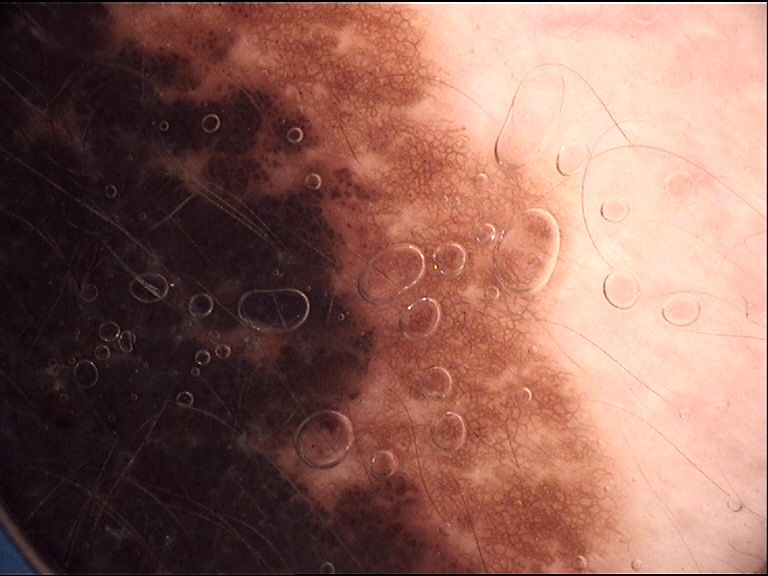  diagnosis:
    name: congenital compound nevus
    code: ccb
    malignancy: benign
    super_class: melanocytic
    confirmation: expert consensus